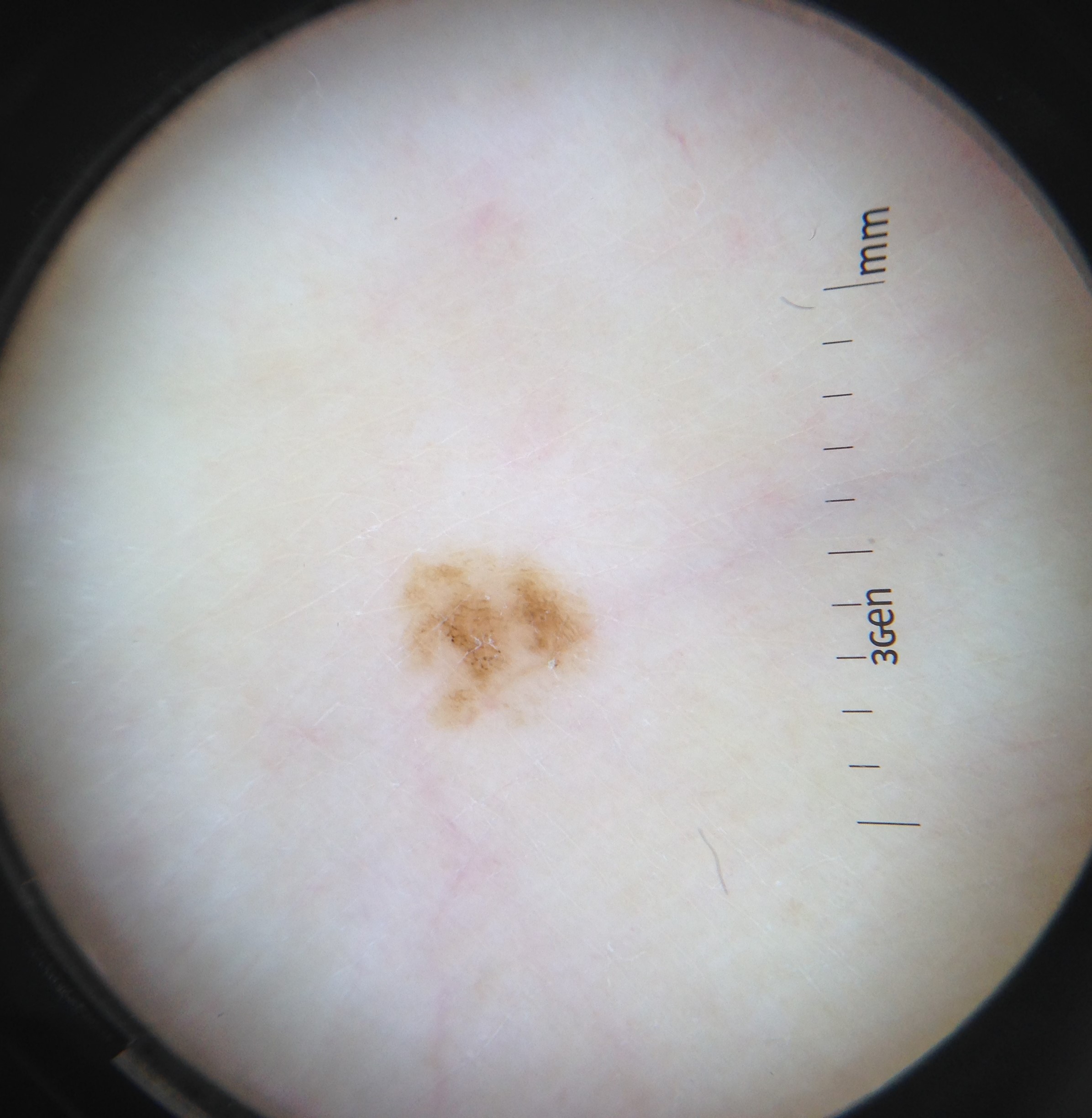Q: What is this lesion?
A: dysplastic junctional nevus (expert consensus)